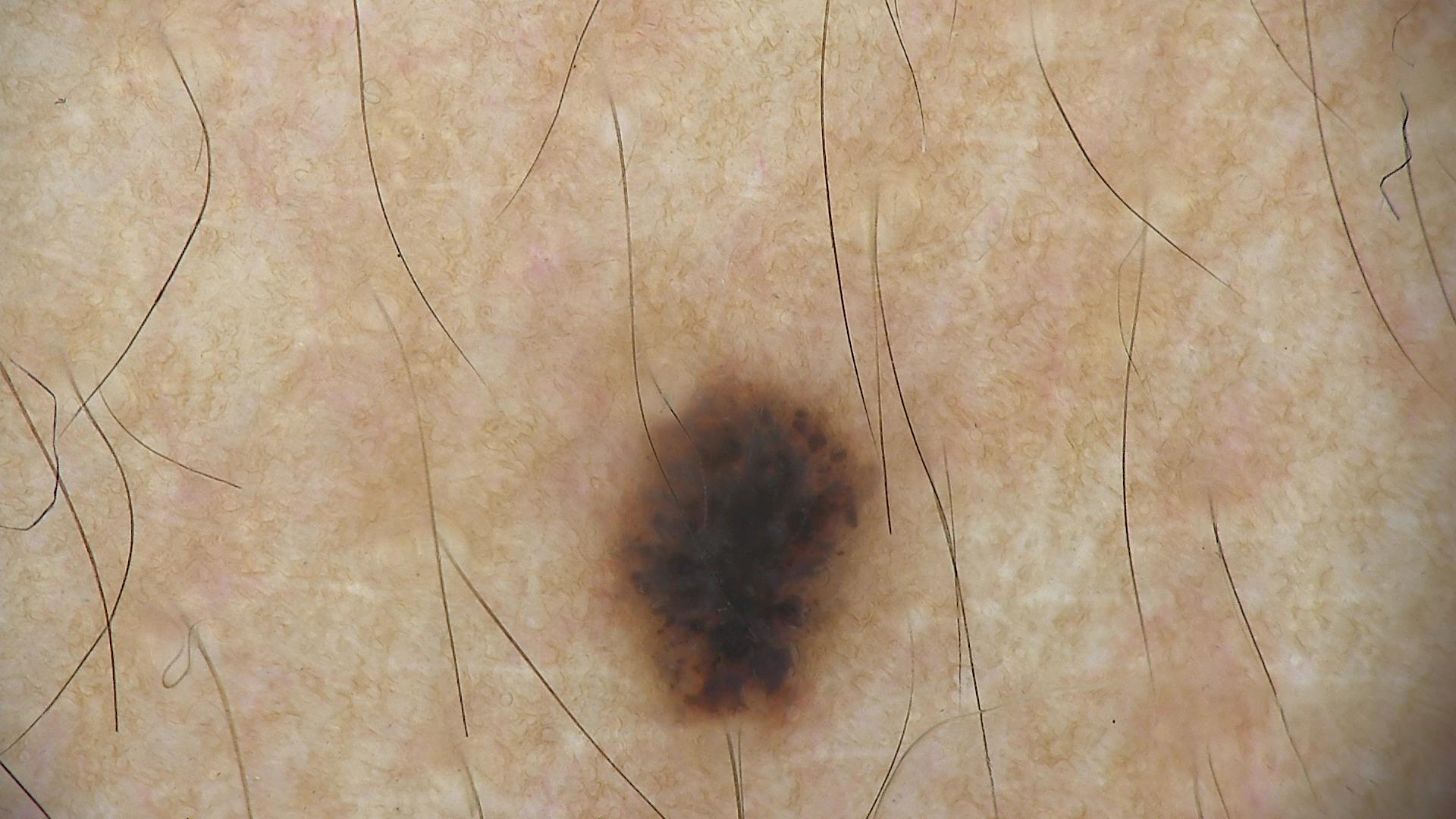Summary:
A dermoscopic photograph of a skin lesion.
Conclusion:
Classified as a dysplastic compound nevus.